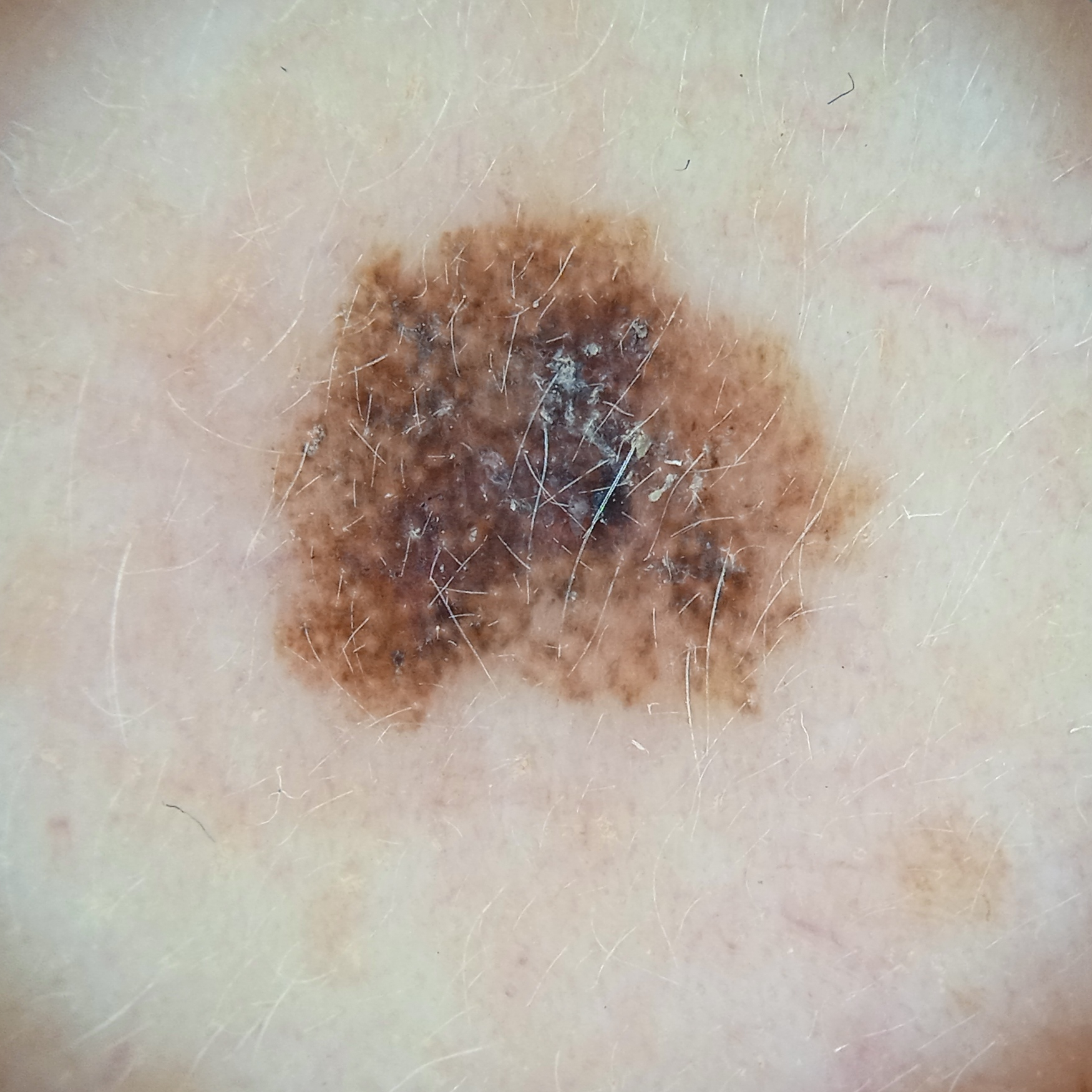Summary: A female subject 50 years old. A dermatoscopic image of a skin lesion. Referred with a clinical suspicion of melanoma. The lesion is located on the face. Measuring roughly 7 mm. Pathology: On biopsy, the diagnosis was a melanoma, following excision, with Breslow depth 0.4 mm.